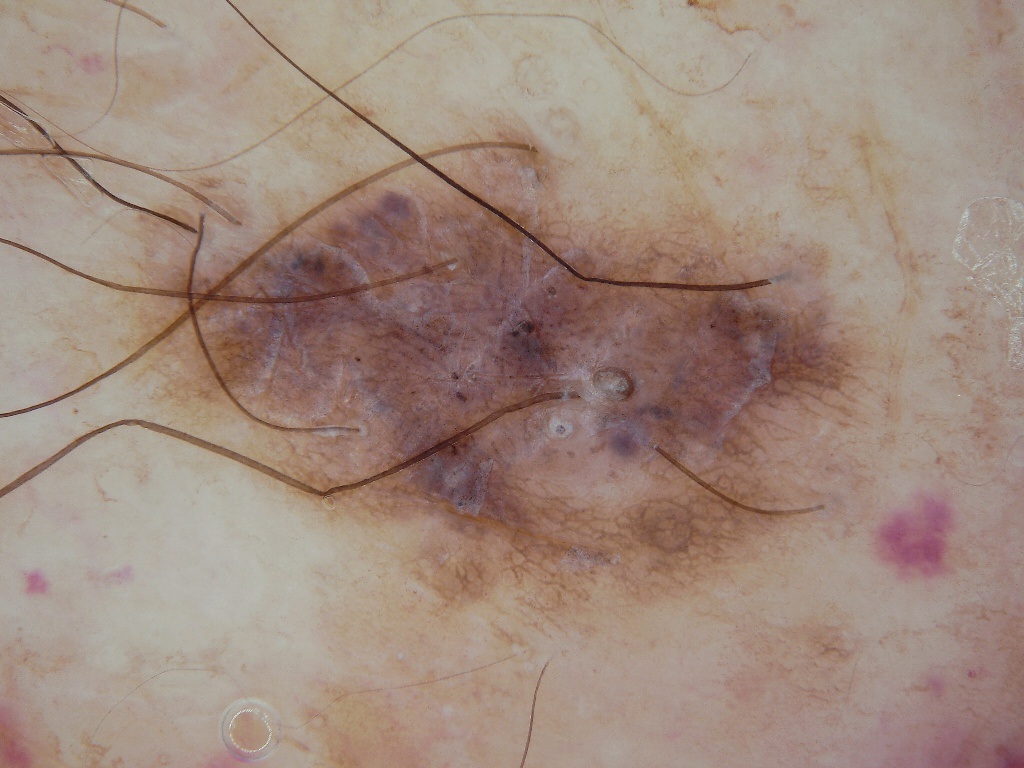  image:
    modality: dermoscopy
  lesion_location:
    bbox_xyxy:
      - 98
      - 105
      - 898
      - 677
  diagnosis:
    name: melanocytic nevus
    malignancy: benign
    lineage: melanocytic
    provenance: clinical